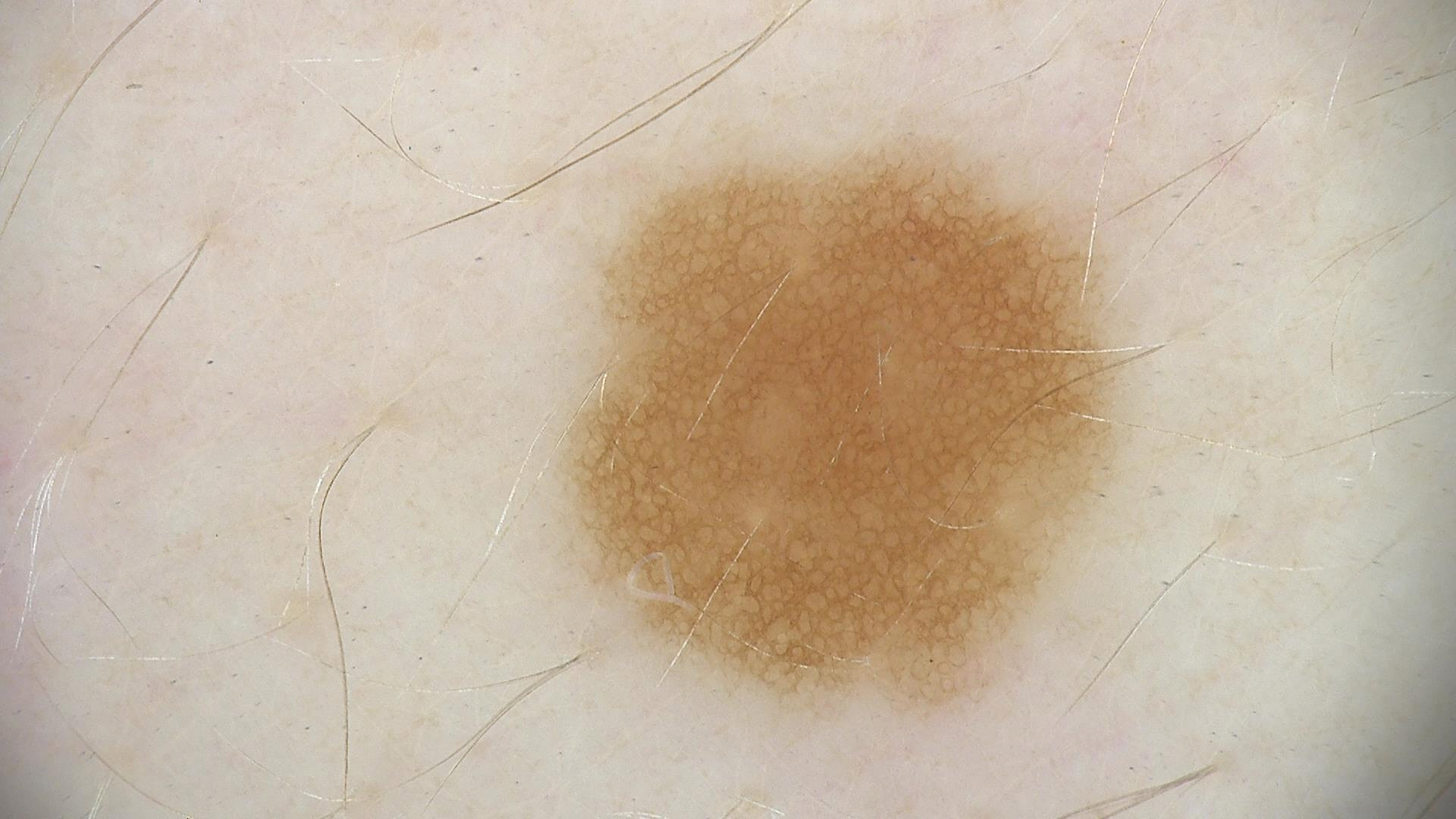diagnosis:
  name: junctional nevus
  code: jb
  malignancy: benign
  super_class: melanocytic
  confirmation: expert consensus